A skin lesion imaged with a dermatoscope.
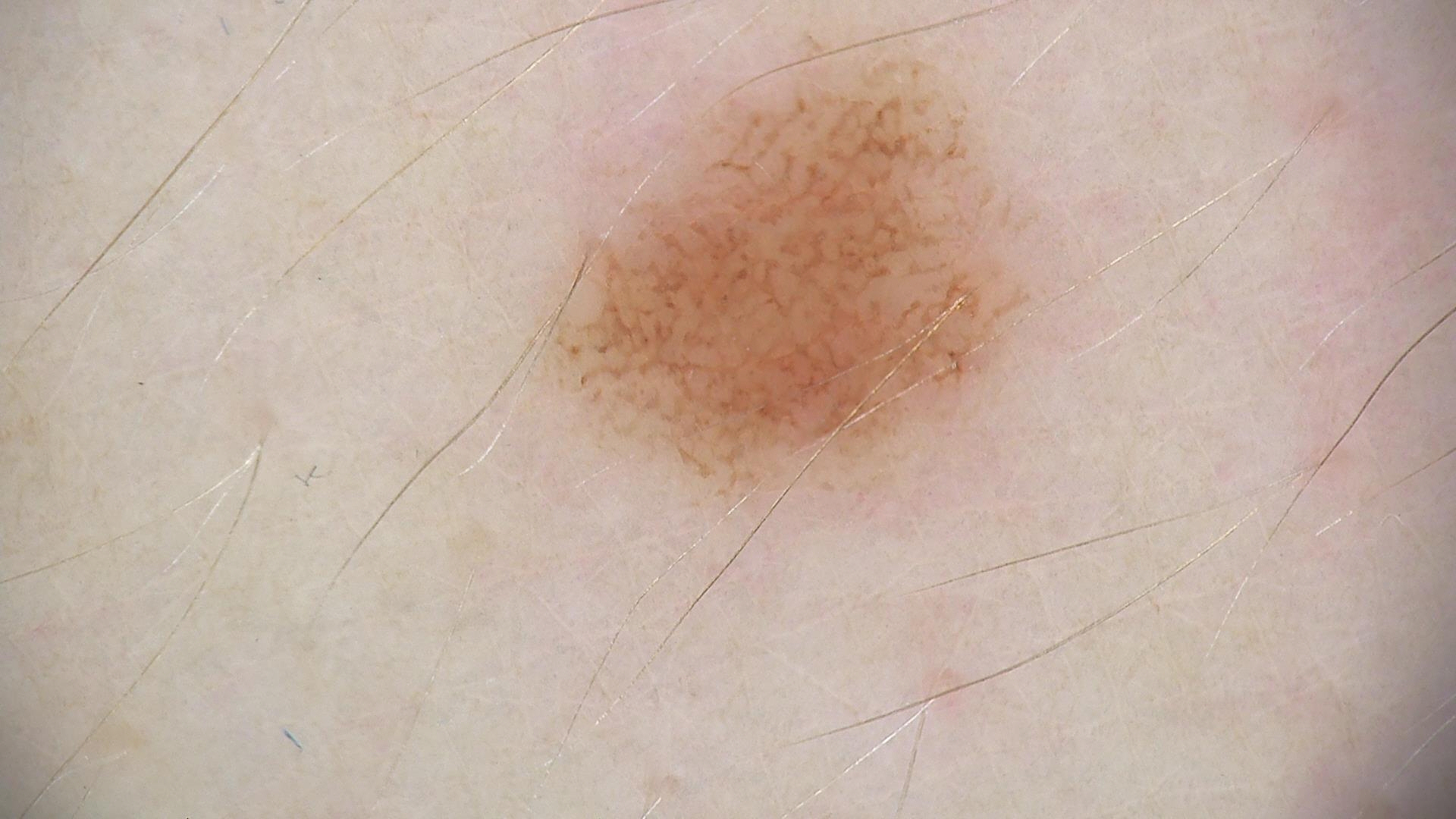diagnosis: dysplastic junctional nevus (expert consensus).